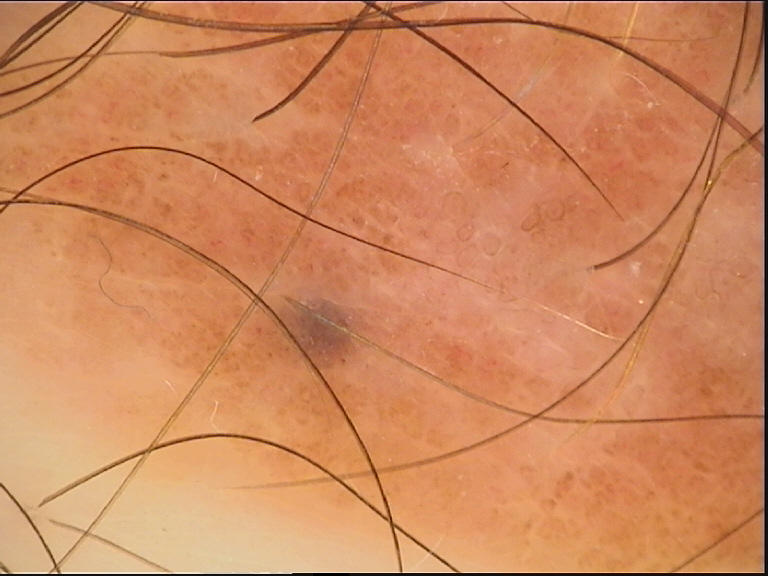label = dysplastic compound nevus (expert consensus).